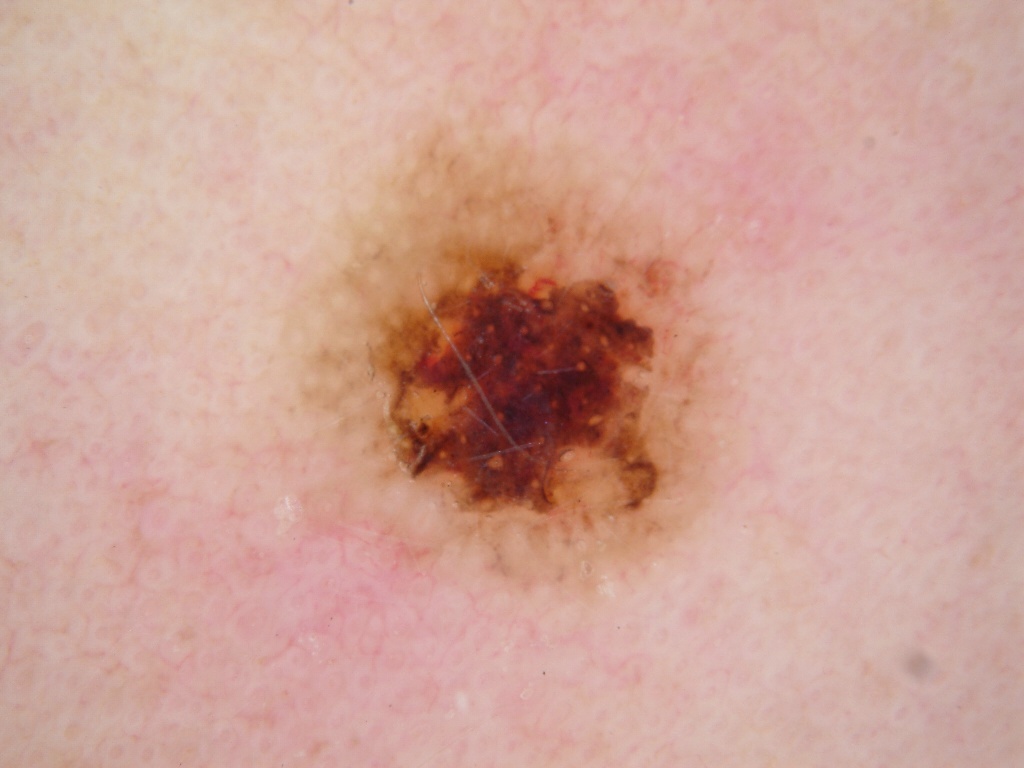Q: Who is the patient?
A: male, aged 8-12
Q: What kind of image is this?
A: dermoscopic image
Q: How large is the lesion within the image?
A: moderate
Q: Where is the lesion located?
A: [248,100,765,604]
Q: What dermoscopic features are not present?
A: globules, pigment network, milia-like cysts, streaks, and negative network
Q: What is the diagnosis?
A: a melanocytic nevus, a benign lesion